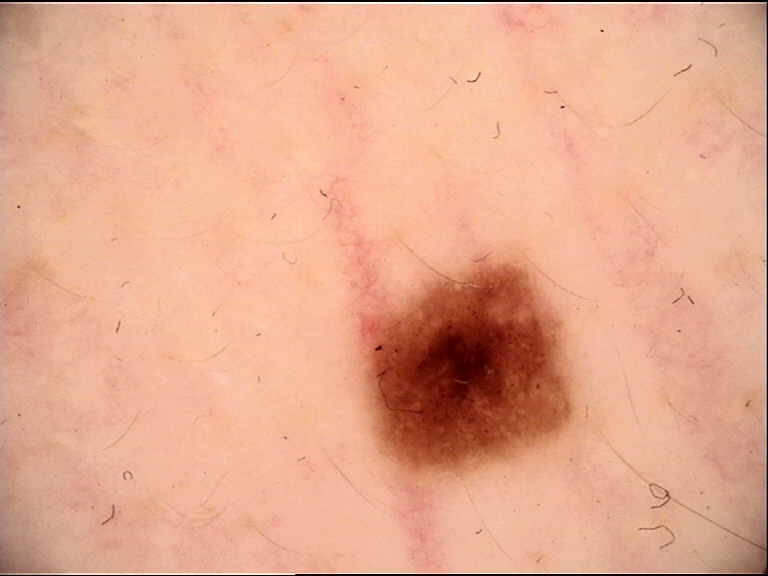diagnosis=dysplastic junctional nevus (expert consensus)